This is a dermoscopic photograph of a skin lesion:
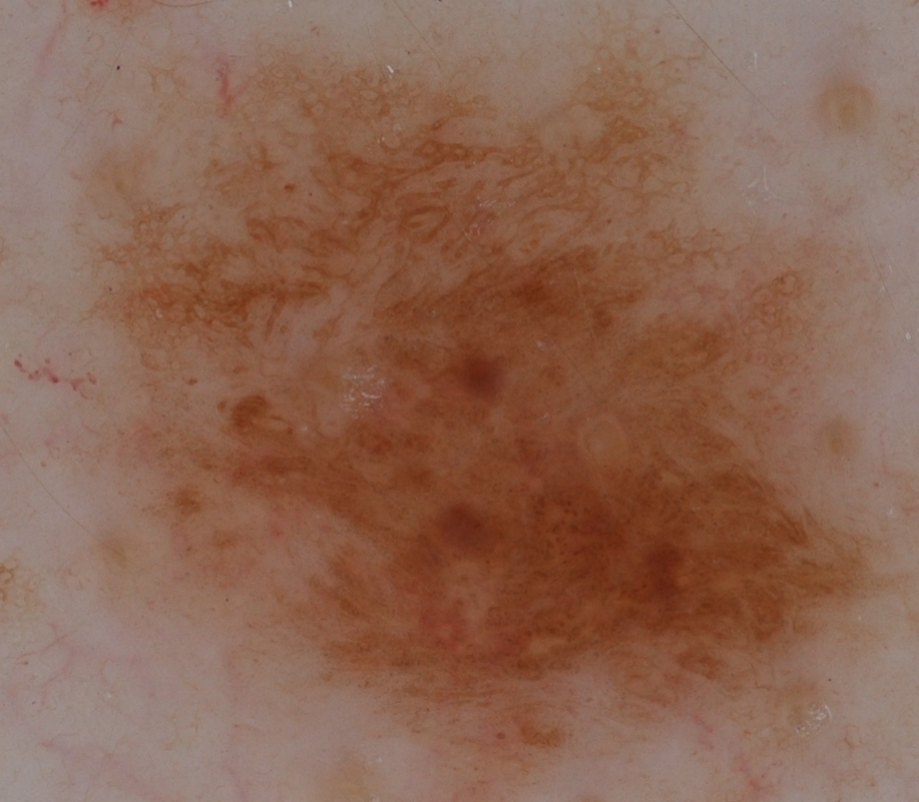bounding box=<bbox>70, 35, 886, 797</bbox> | lesion size=~62% of the field | features=globules and pigment network; absent: streaks, negative network, and milia-like cysts | assessment=a melanocytic nevus, a benign lesion.